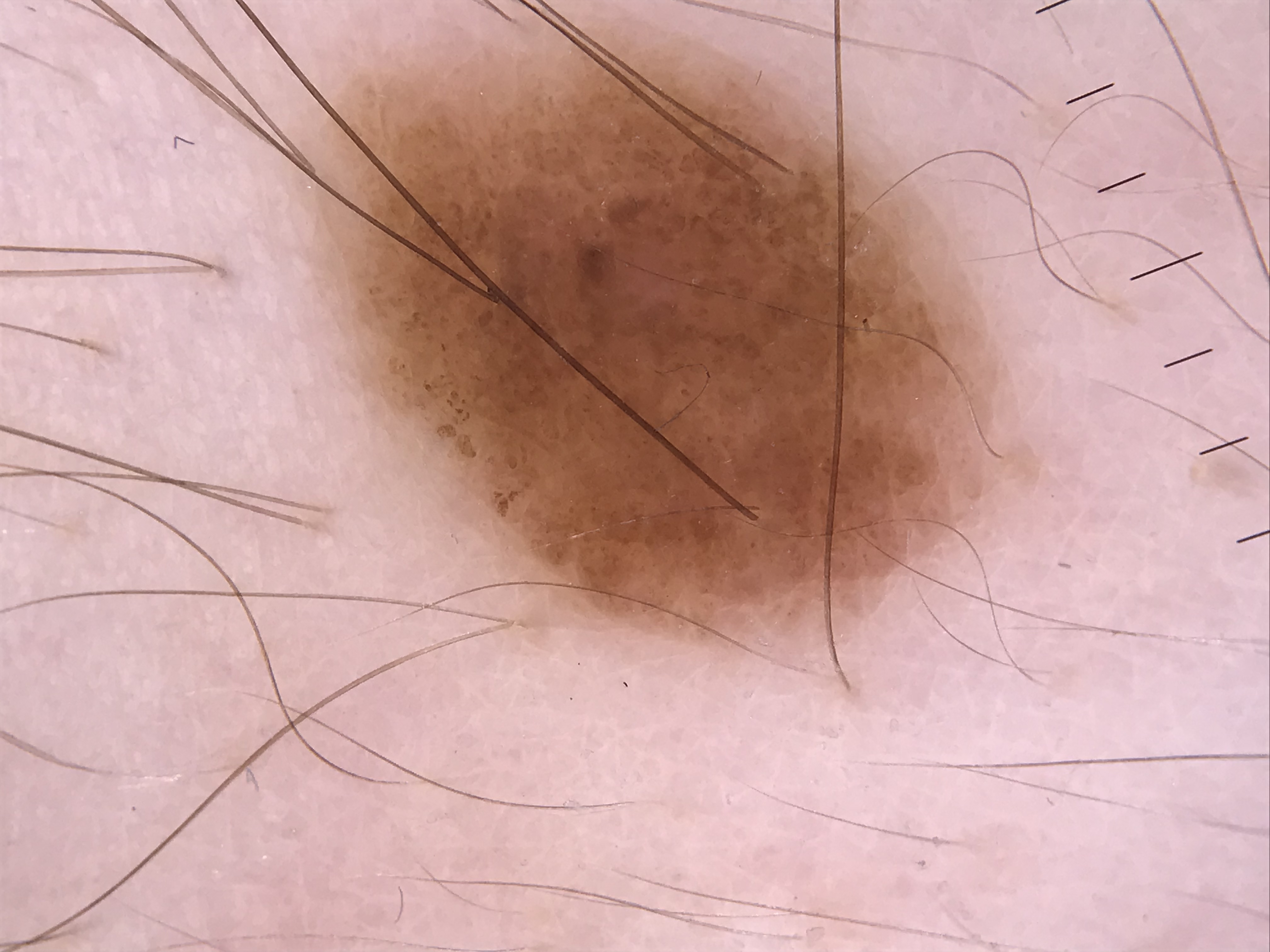Q: What is this lesion?
A: compound nevus (expert consensus)